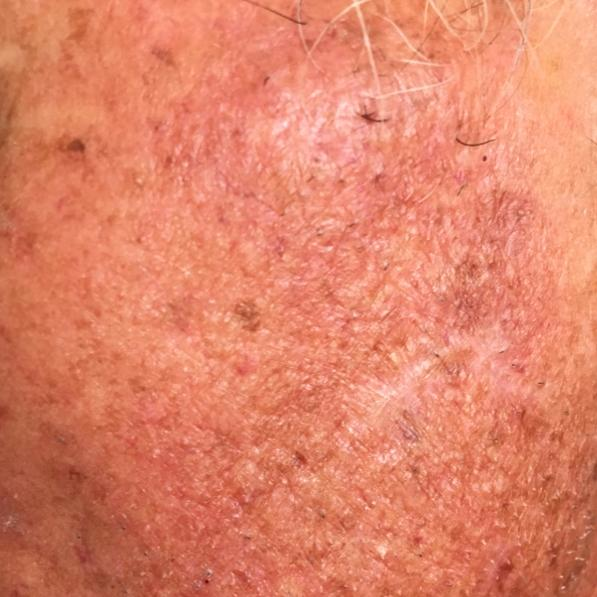<lesion>
  <patient>
    <age>55</age>
  </patient>
  <image>smartphone clinical photo</image>
  <lesion_location>the face</lesion_location>
  <diagnosis>
    <name>actinic keratosis</name>
    <code>ACK</code>
    <malignancy>indeterminate</malignancy>
    <confirmation>clinical consensus</confirmation>
  </diagnosis>
</lesion>